The photo was captured at an angle. Male contributor, age 50–59. The patient considered this a rash. The lesion is associated with itching. Reported duration is less than one week. The lesion involves the back of the hand and arm: 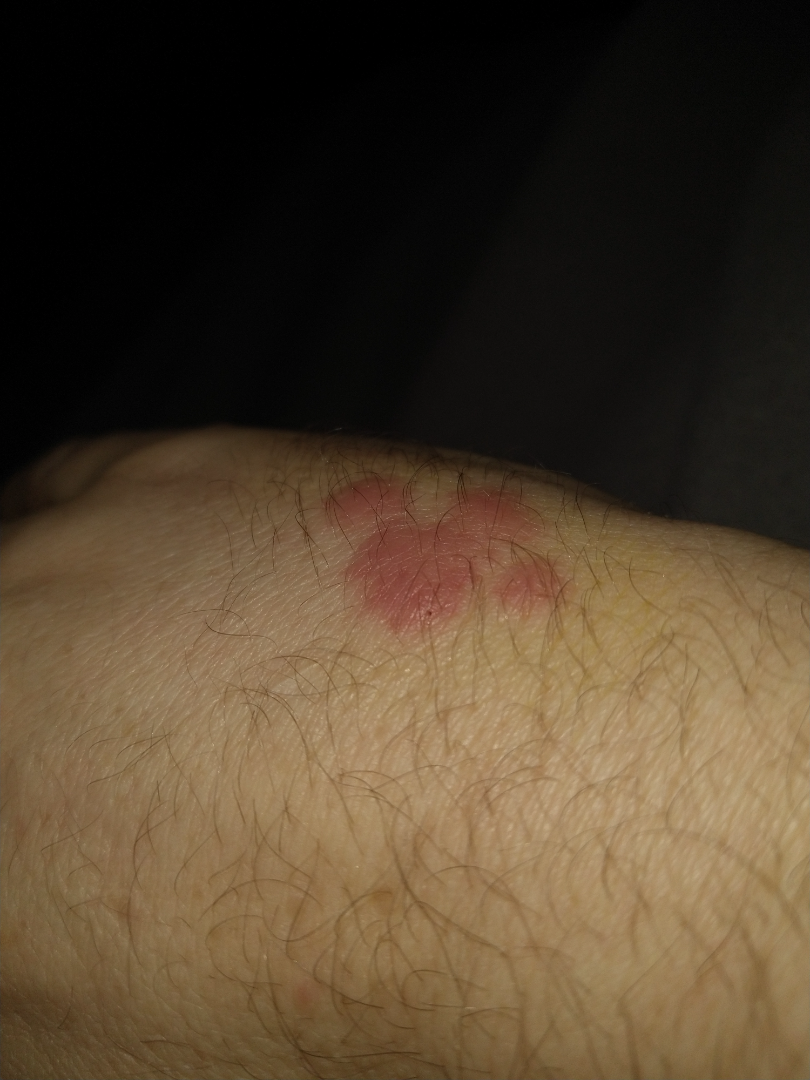clinical impression = the differential is split between Cutaneous sarcoidosis, Skin and soft tissue atypical mycobacterial infection and Granuloma annulare; less probable is Insect Bite; a more distant consideration is B-Cell Cutaneous Lymphoma.